No constitutional symptoms were reported. Reported duration is less than one week. Skin tone: lay graders estimated 3 on the Monk Skin Tone. The subject is 30–39, female. The arm is involved. The lesion is described as raised or bumpy. Close-up view. Symptoms reported: itching, bothersome appearance, enlargement and pain. The patient considered this a rash.
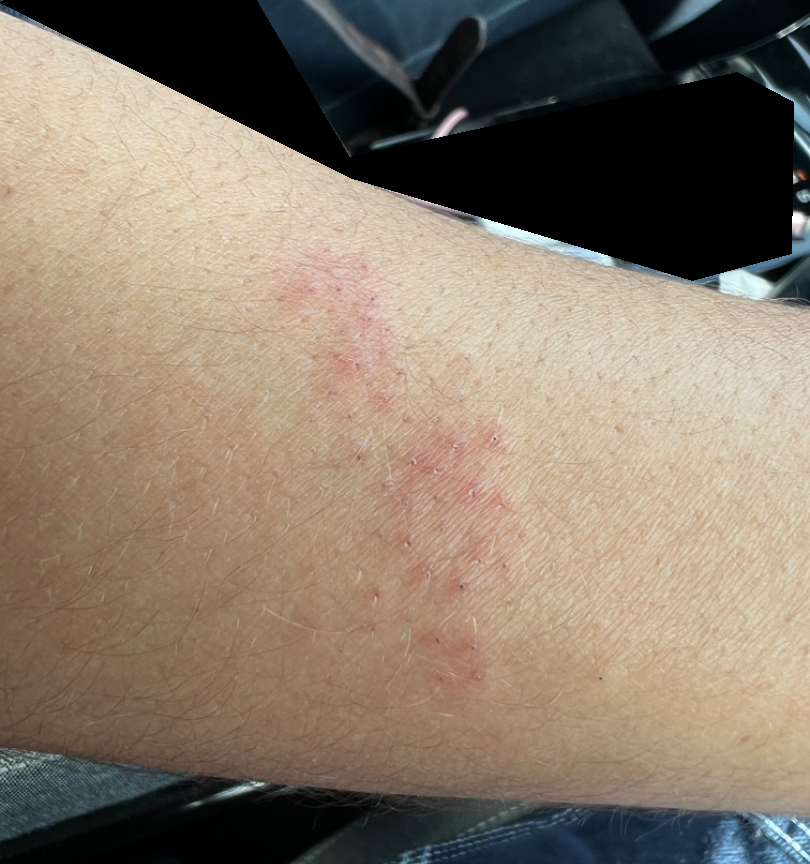On remote dermatologist review, Irritant Contact Dermatitis (0.67); Folliculitis (0.33).